The condition has been present for one to four weeks, this is a close-up image, self-categorized by the patient as a rash, the subject is a female aged 18–29, located on the head or neck.
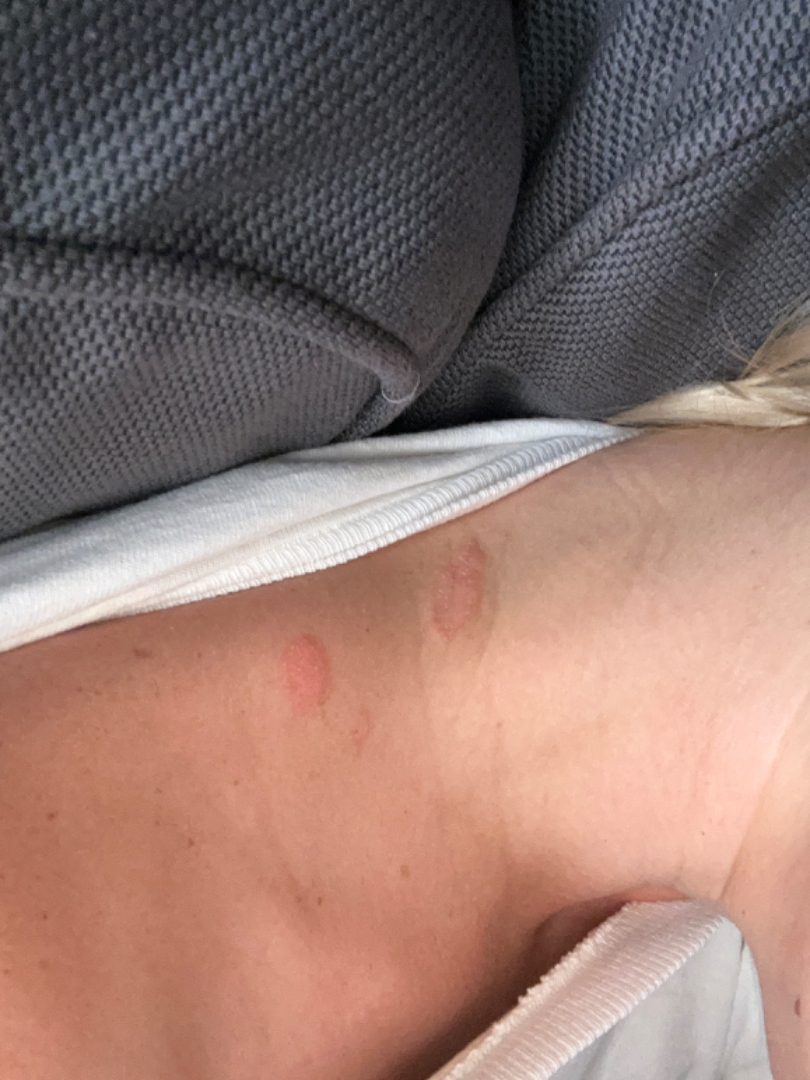Review:
On dermatologist assessment of the image: most likely Pityriasis rosea; the differential also includes Eczema; a remote consideration is Syphilis.